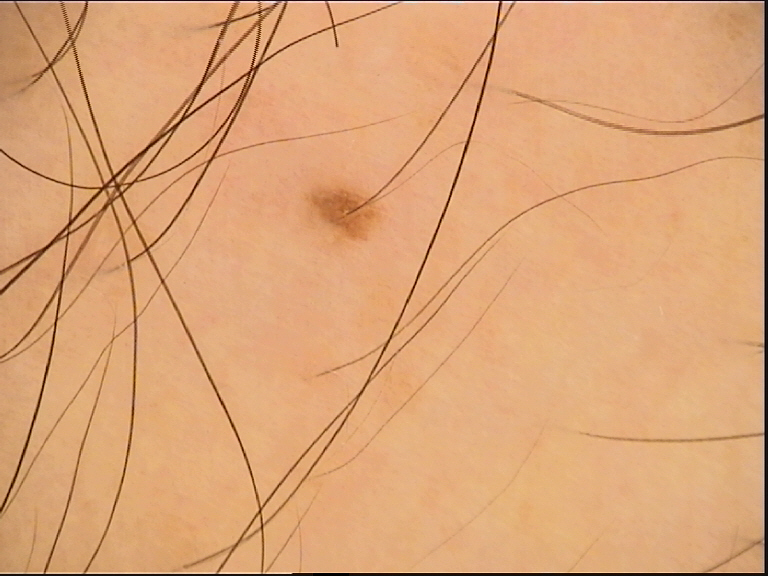This is a banal lesion. Consistent with a junctional nevus.